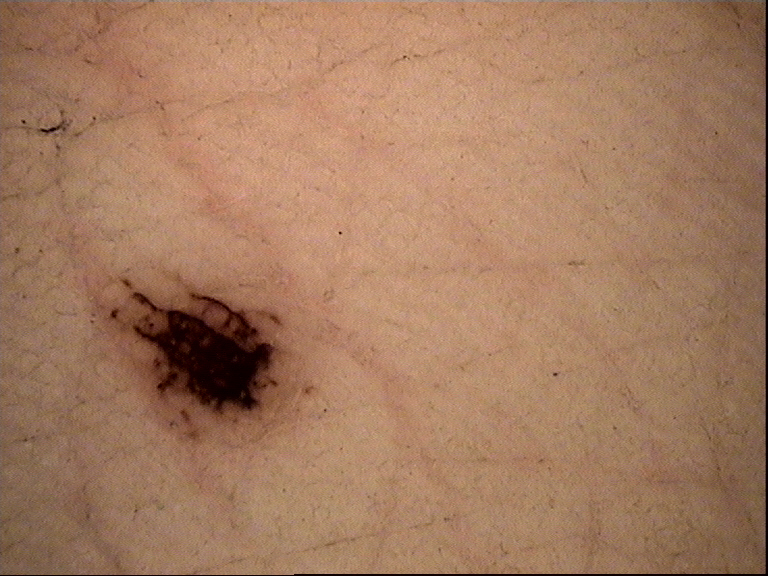diagnosis = acral dysplastic junctional nevus (expert consensus).